The photograph was taken at an angle.
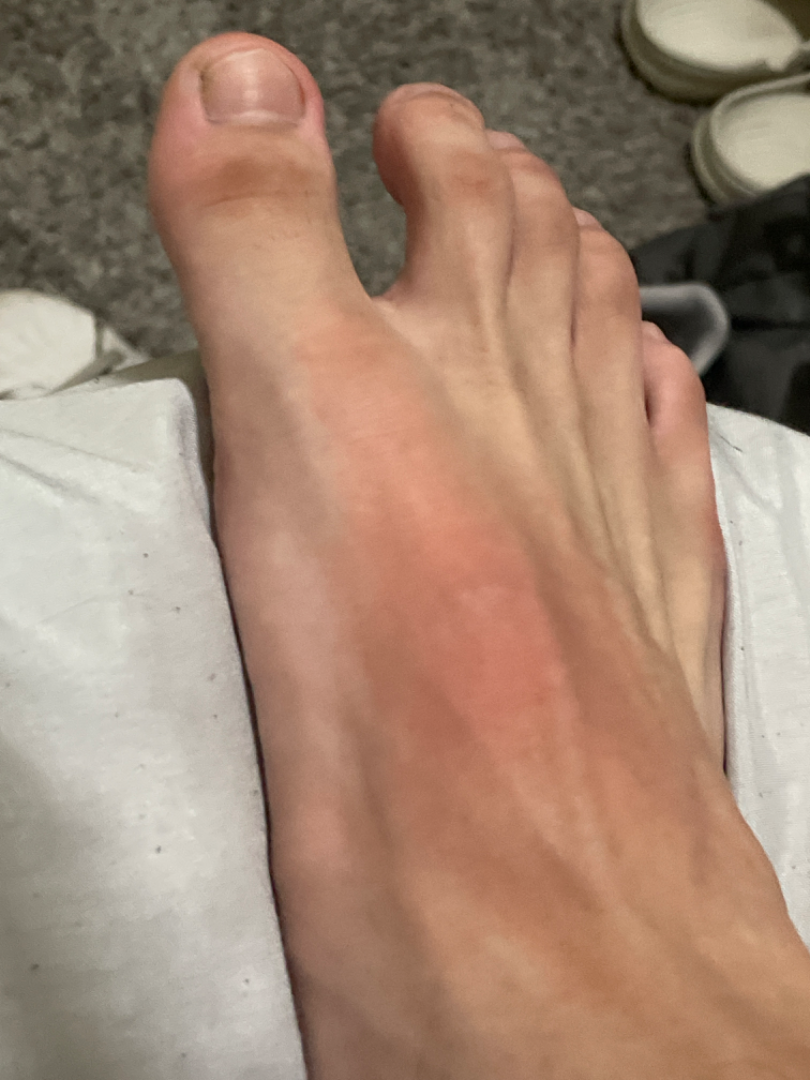  assessment: indeterminate